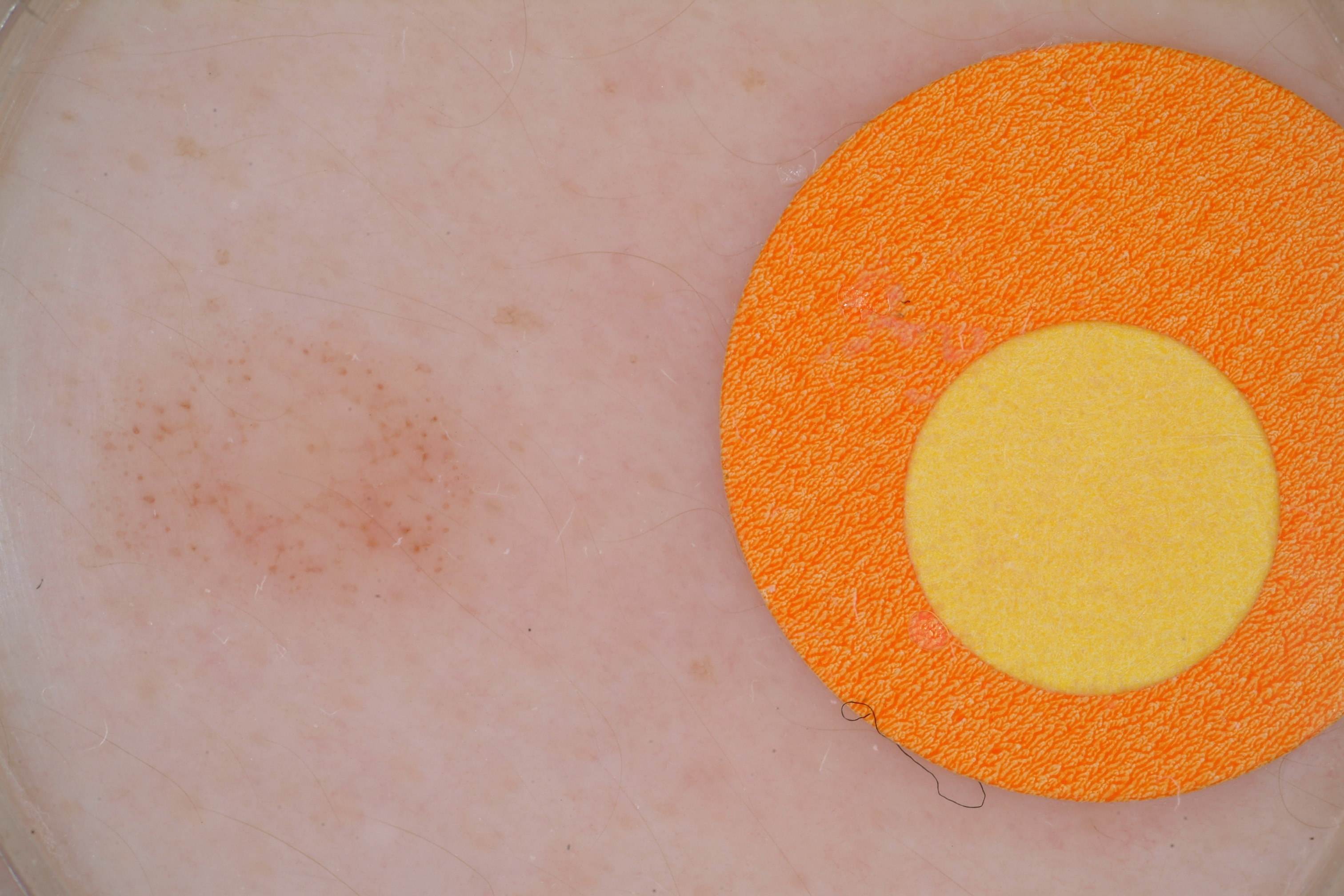A dermoscopic view of a skin lesion. The patient is a male aged 13 to 17. The visible lesion spans left=63, top=298, right=526, bottom=633. The lesion occupies roughly 11% of the field. Dermoscopically, the lesion shows globules; no negative network, streaks, pigment network, or milia-like cysts. Consistent with a melanocytic nevus.